The photograph is a close-up of the affected area; the back of the hand, leg, head or neck, back of the torso, arm, front of the torso and palm are involved; self-categorized by the patient as skin that appeared healthy to them; reported lesion symptoms include itching and burning; the subject is 18–29, male:
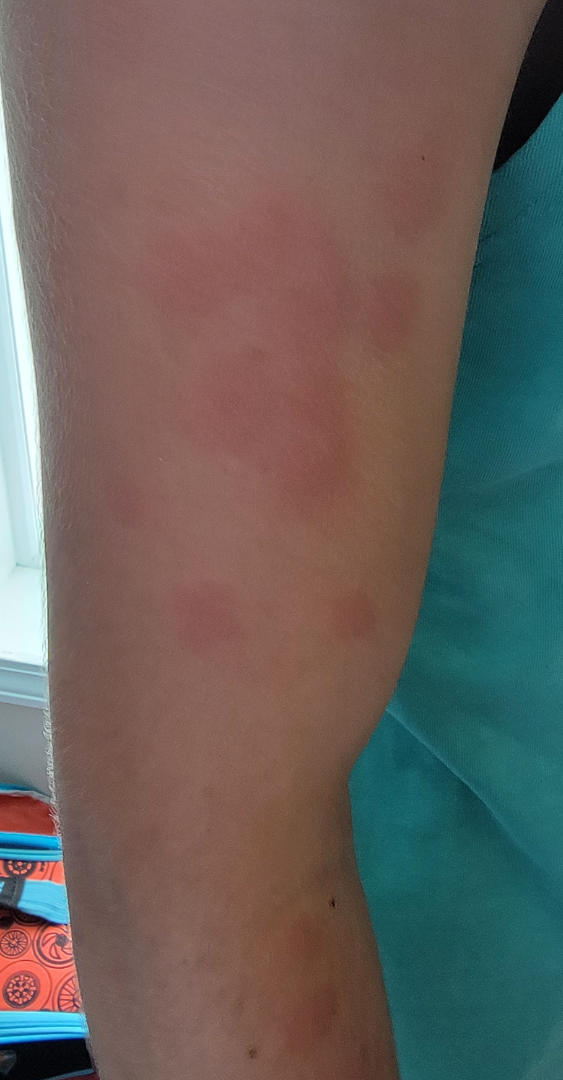In keeping with Urticaria.